A skin lesion imaged with a dermatoscope.
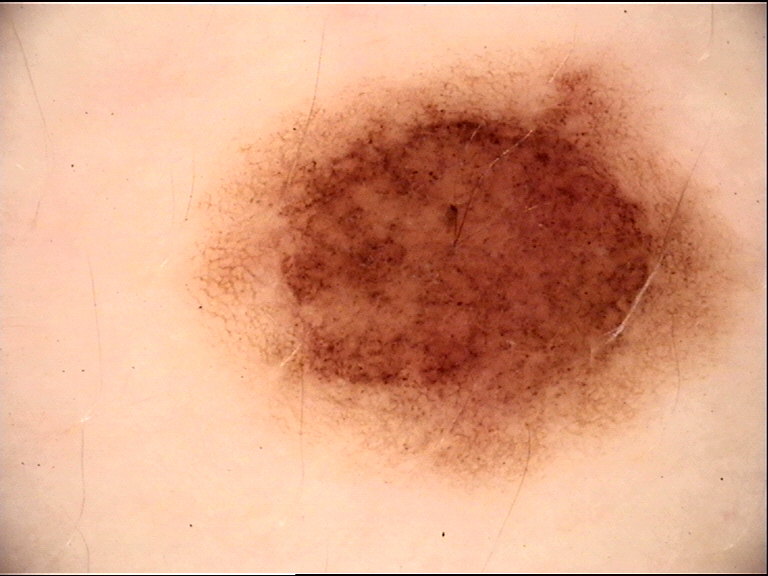assessment: dysplastic compound nevus (expert consensus).